The photograph is a close-up of the affected area:
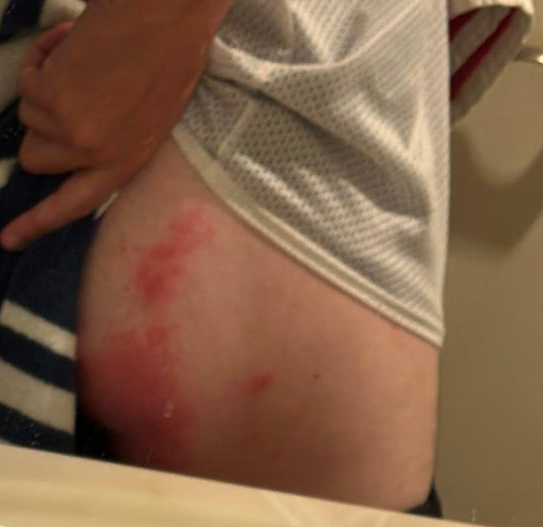The case was difficult to assess from the available photograph.